A dermoscopic image of a skin lesion.
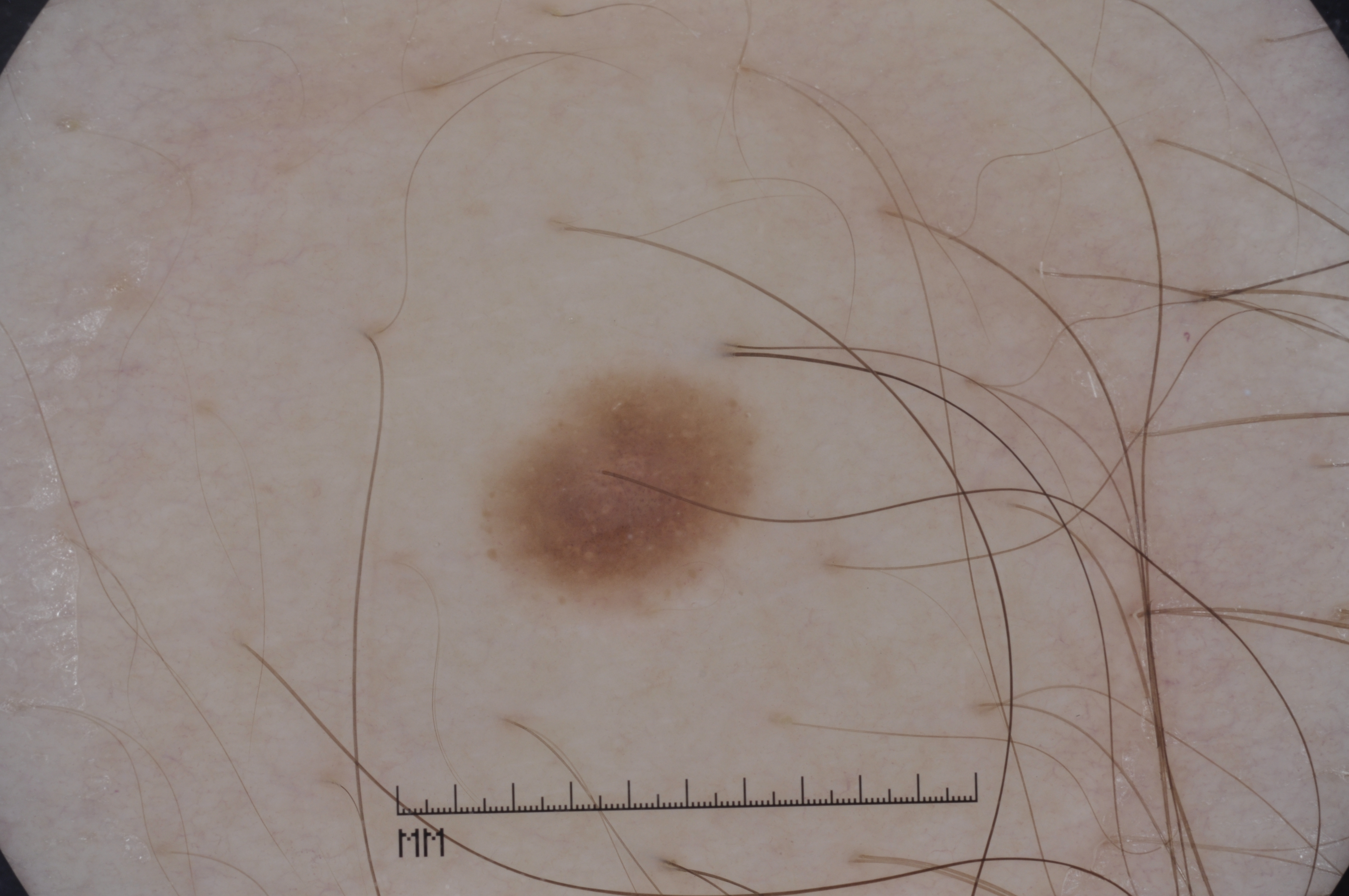Findings:
Dermoscopy demonstrates milia-like cysts, with no pigment network, streaks, or negative network. In (x1, y1, x2, y2) order, the lesion spans [485,371,759,602].
Conclusion:
Diagnosed as a melanocytic nevus, a benign lesion.